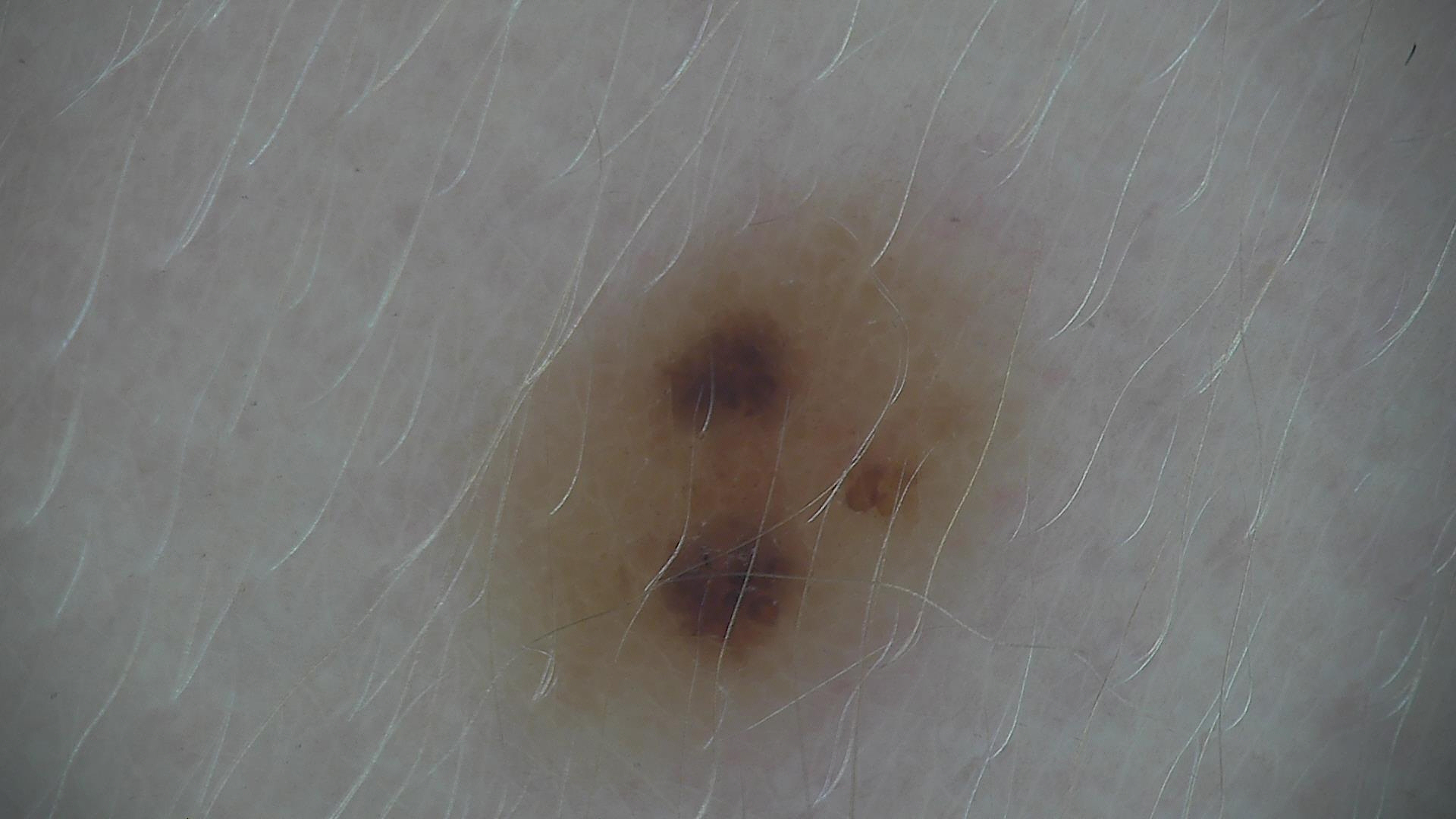  lesion_type:
    main_class: banal
    pattern: compound
  diagnosis:
    name: compound nevus
    code: cb
    malignancy: benign
    super_class: melanocytic
    confirmation: expert consensus